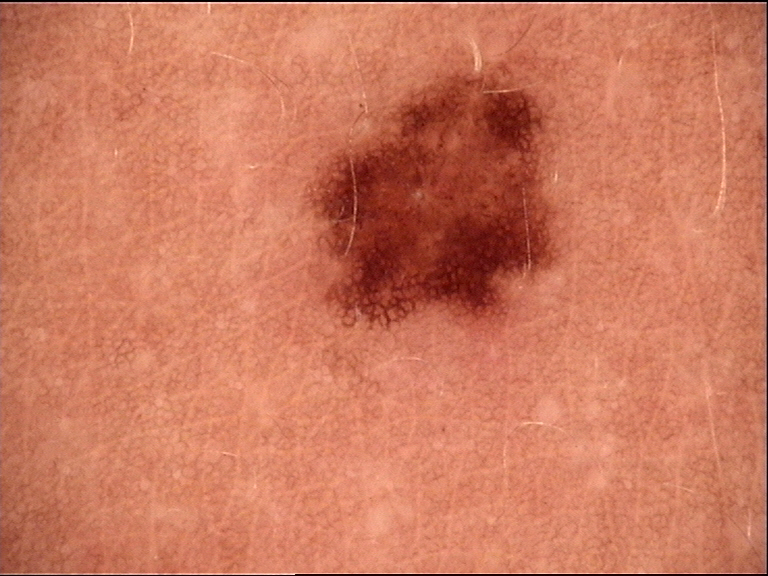Q: What is the imaging modality?
A: dermoscopy
Q: What was the diagnostic impression?
A: dysplastic junctional nevus (expert consensus)